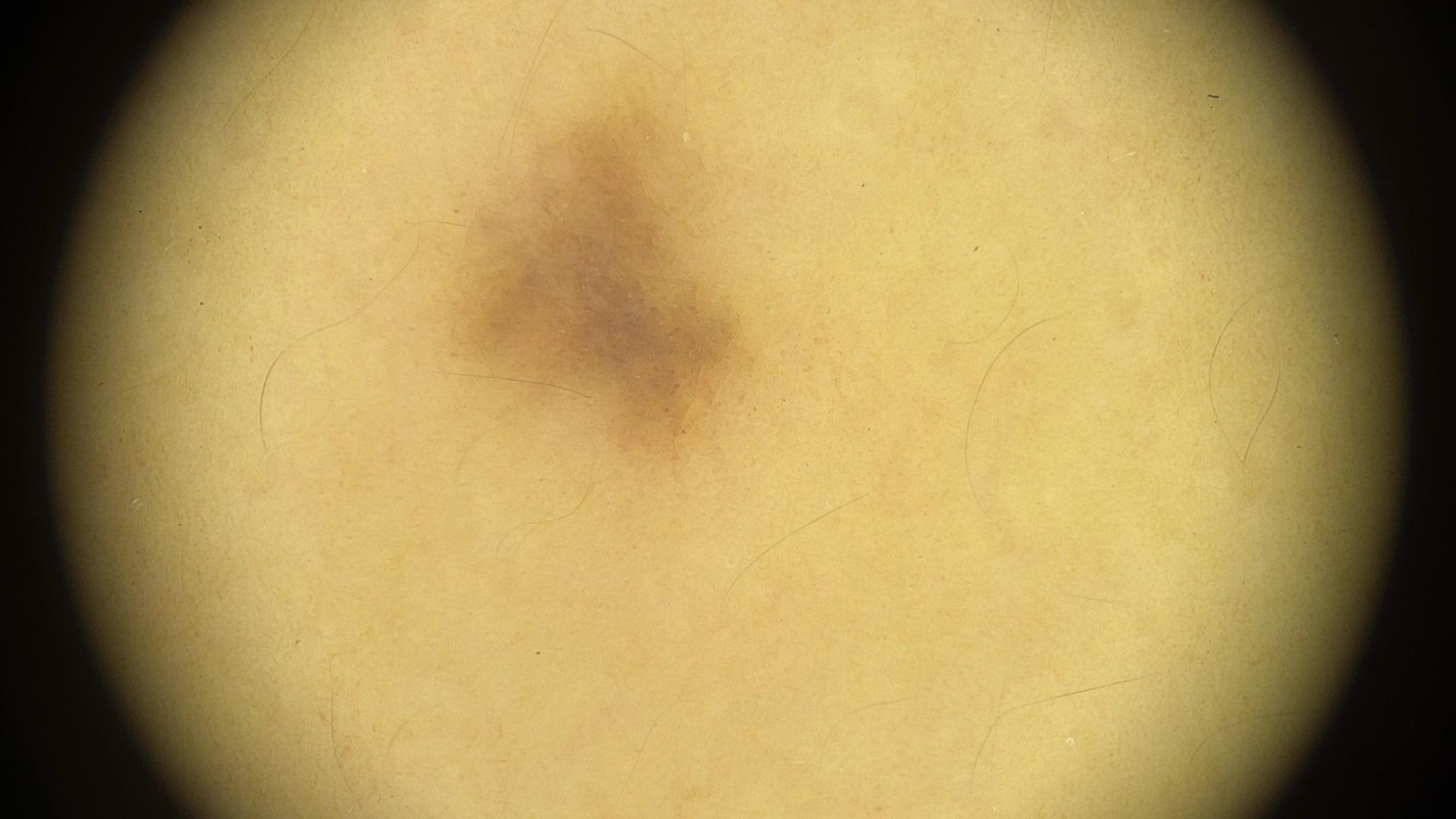{"diagnosis": {"name": "Nevus", "malignancy": "benign", "confirmation": "expert clinical impression", "lineage": "melanocytic"}}